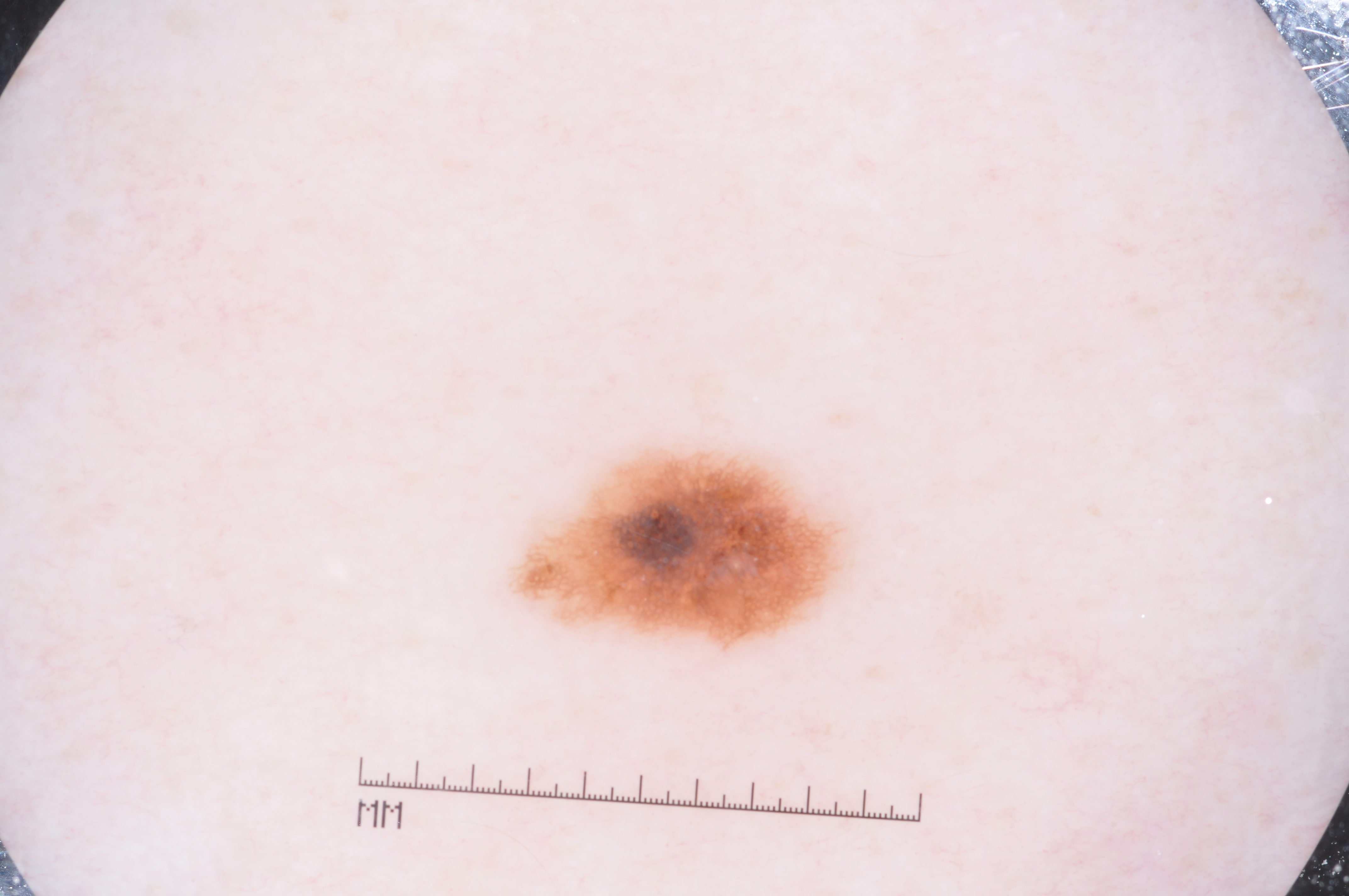Image and clinical context: A male patient, aged approximately 50. A dermoscopic close-up of a skin lesion. The dermoscopic pattern shows milia-like cysts and pigment network, with no negative network or streaks. The lesion occupies roughly 4% of the field. The lesion's extent is x1=510, y1=447, x2=847, y2=652. Diagnosis: Histopathology confirmed a melanoma, a skin cancer.